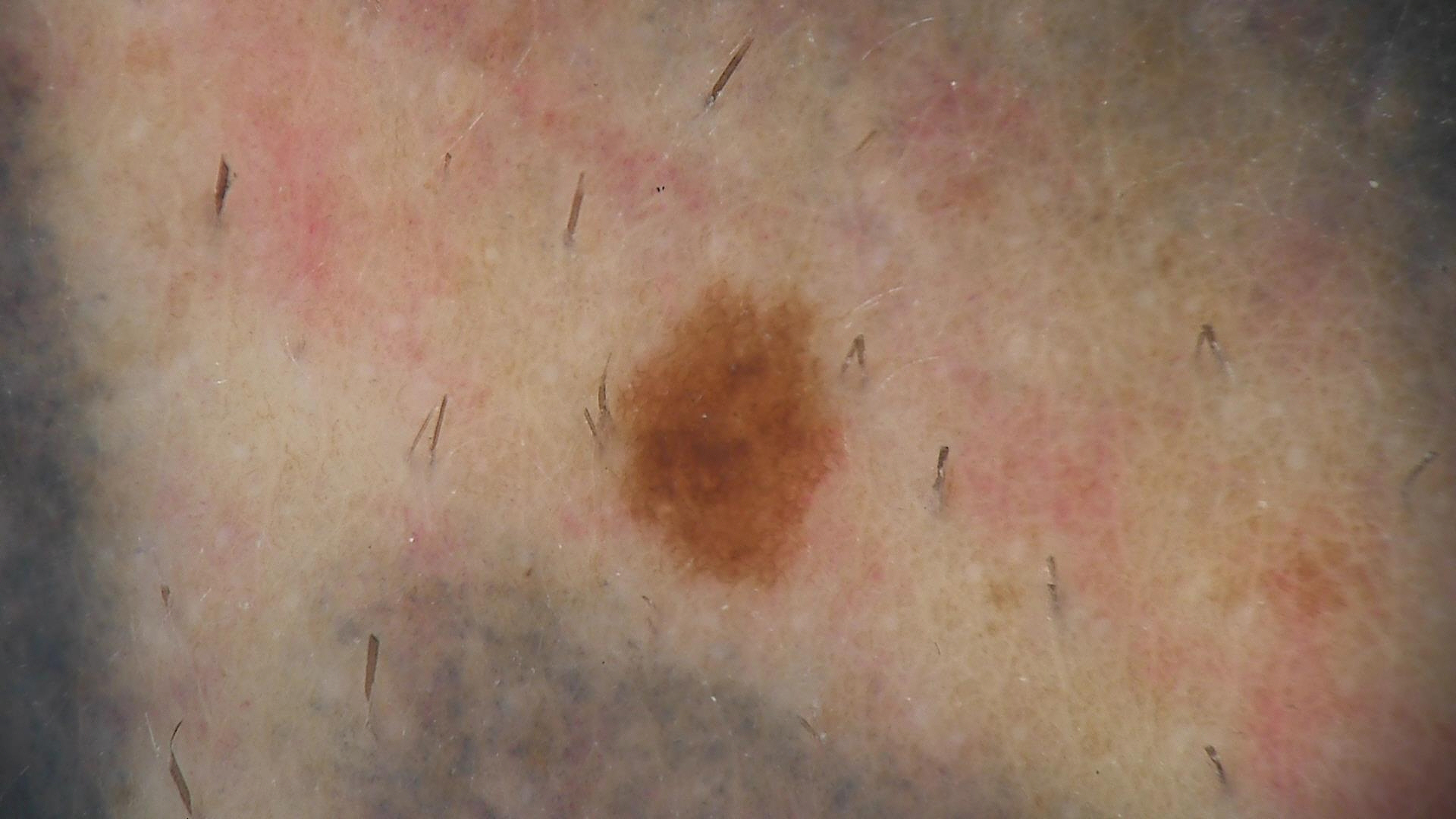A dermoscopic close-up of a skin lesion. Labeled as a dysplastic junctional nevus.